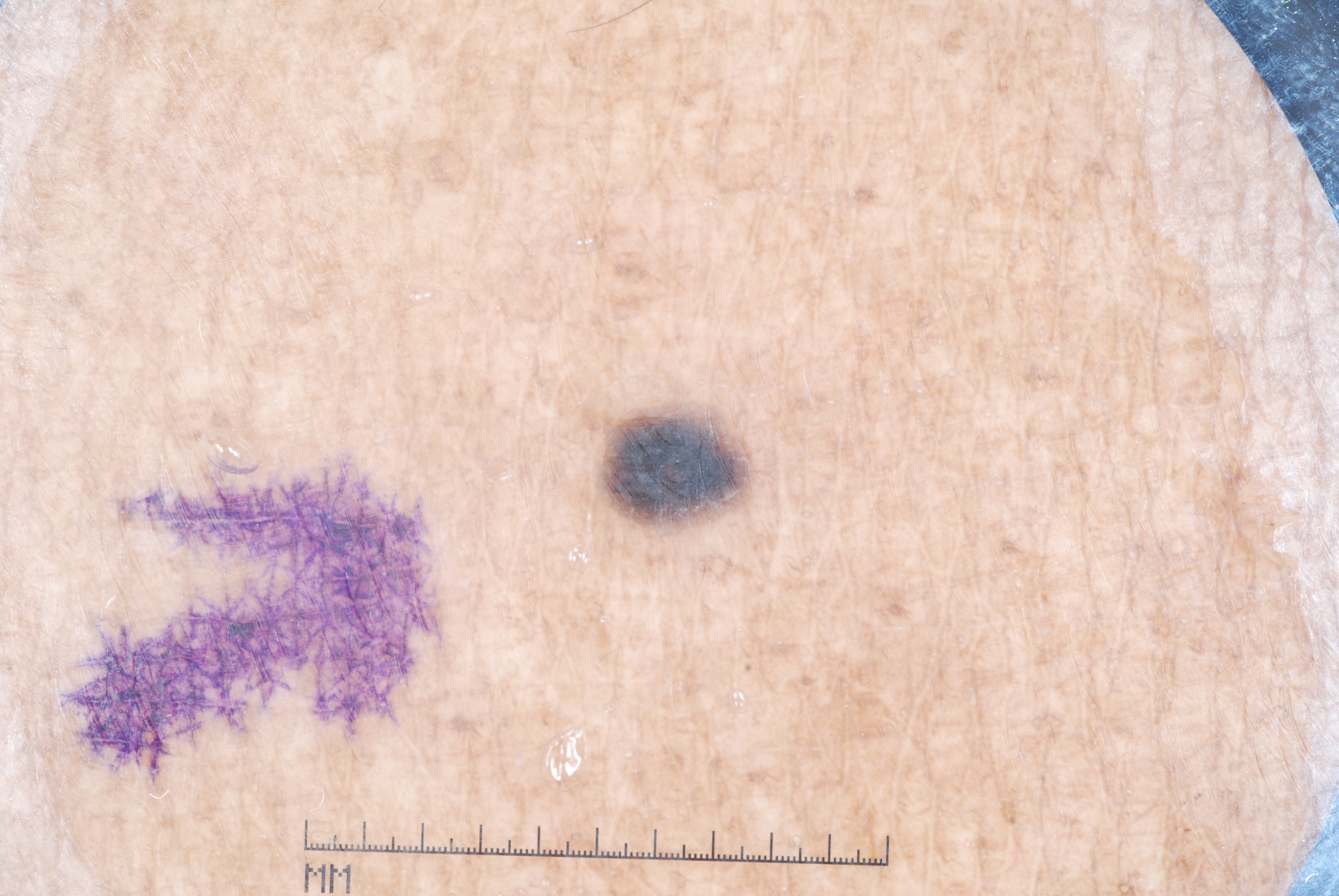The subject is a female aged around 75. A dermoscopic image of a skin lesion. The lesion's extent is [586,406,732,525]. The dermoscopic pattern shows milia-like cysts. The clinical diagnosis was a seborrheic keratosis.